The contributor is a female aged 40–49; the lesion involves the front of the torso and arm; an image taken at a distance — 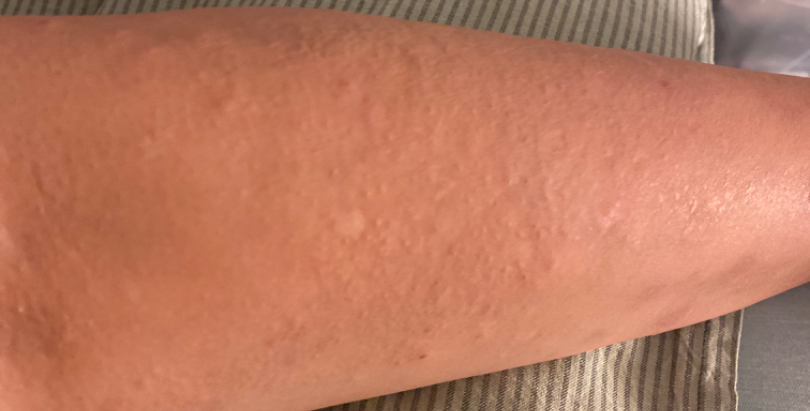Q: What is the dermatologist's impression?
A: Folliculitis (35%); Tinea (22%); Eczema (22%); Lichen Simplex Chronicus (22%)